The lesion involves the back of the hand. Female subject, age 30–39. Reported duration is less than one week. The patient indicates the lesion is fluid-filled, raised or bumpy and rough or flaky. The patient indicates associated joint pain and fatigue. Reported lesion symptoms include burning, pain, enlargement, bothersome appearance and itching. Close-up view. Self-categorized by the patient as a rash: 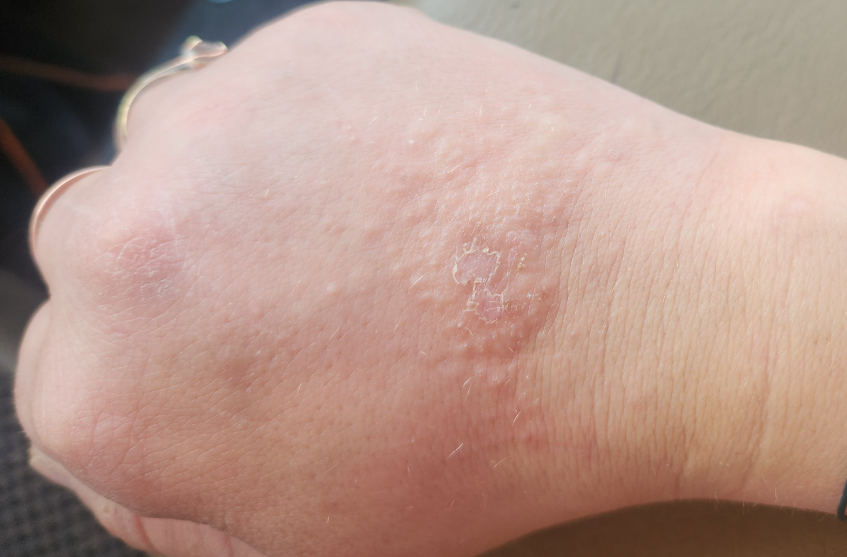<summary>
<differential>
  <leading>Eczema</leading>
  <considered>Irritant Contact Dermatitis</considered>
  <unlikely>Allergic Contact Dermatitis</unlikely>
</differential>
</summary>